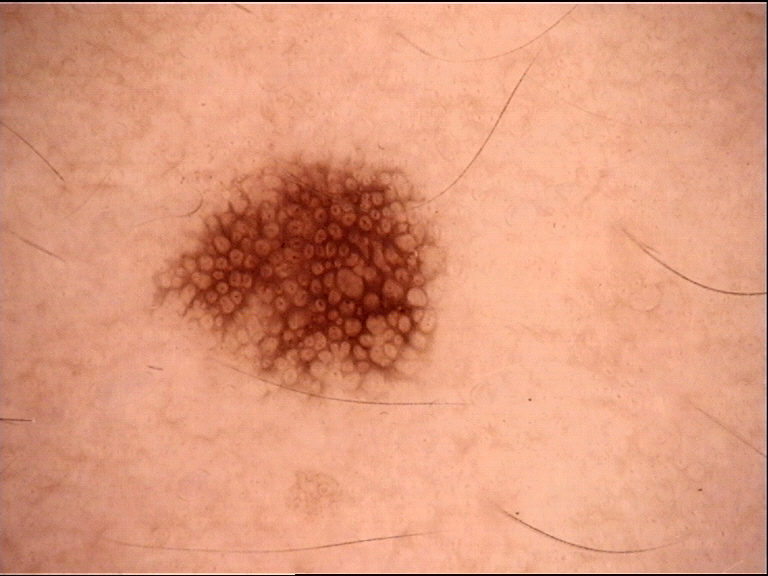assessment — dysplastic junctional nevus (expert consensus)